This is a close-up image · present for less than one week · female patient, age 50–59 · the lesion involves the palm · the lesion is described as rough or flaky and raised or bumpy.
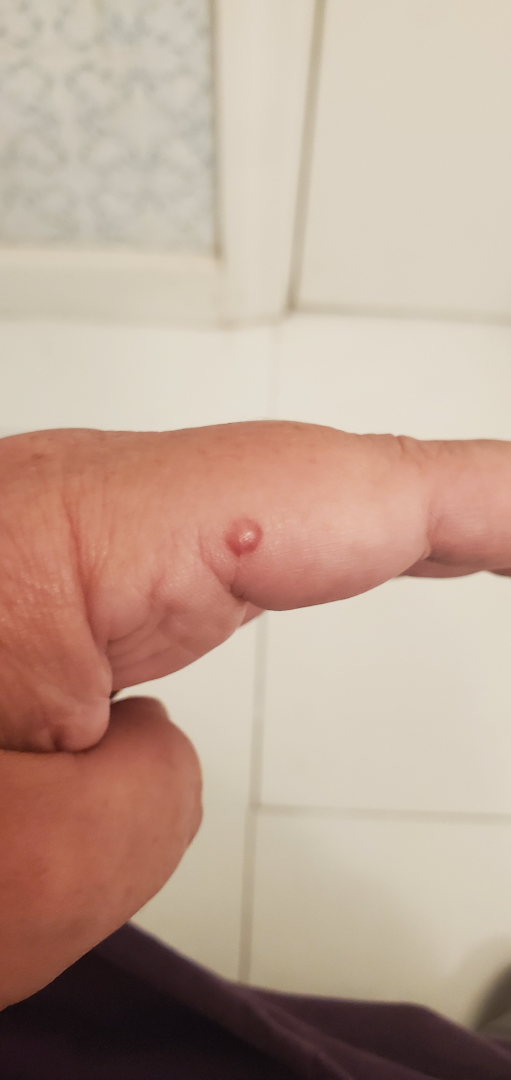Assessment: The condition could not be reliably identified from the image.